A dermoscopic close-up of a skin lesion: 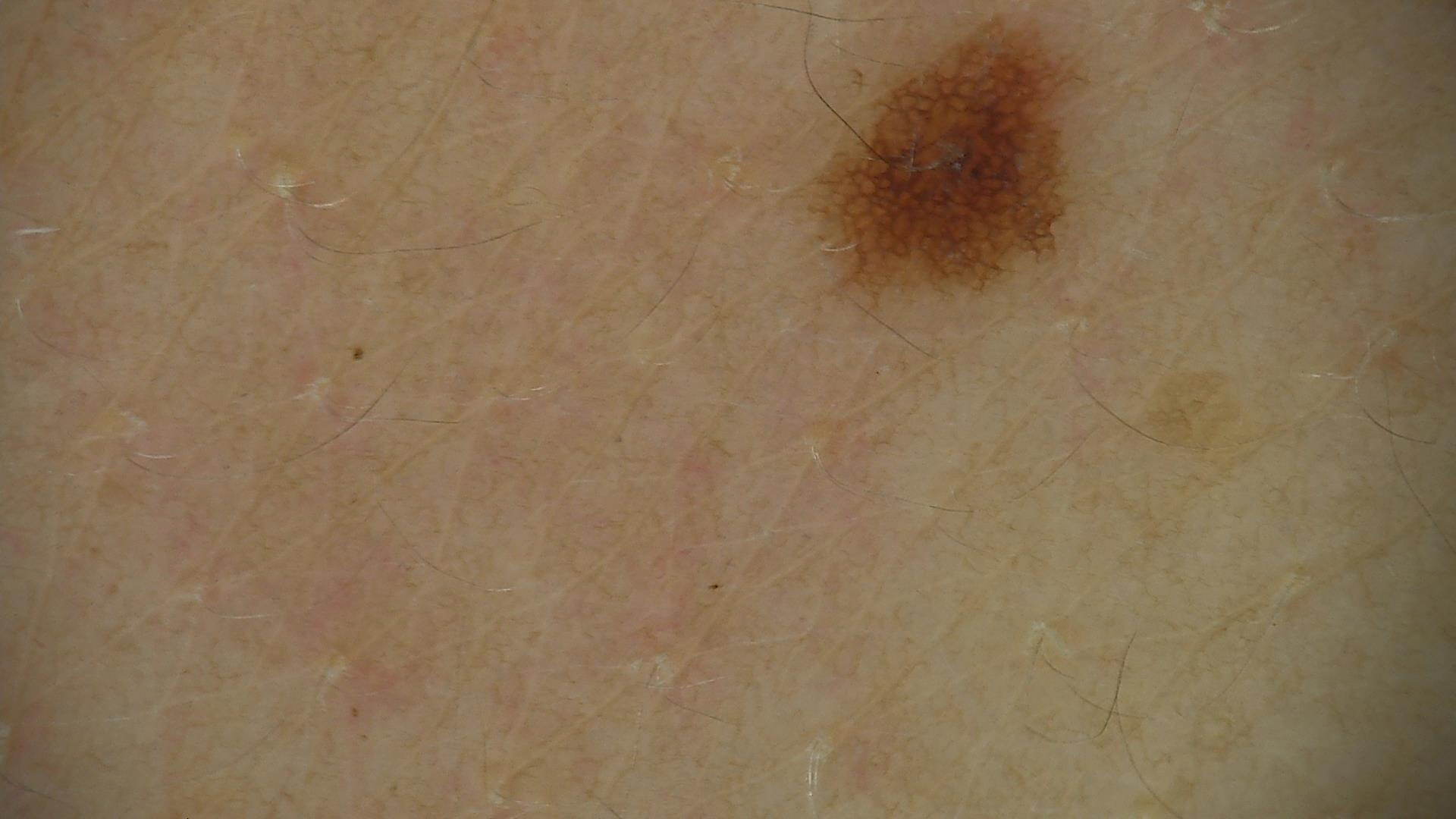Classified as a benign lesion — a dysplastic junctional nevus.